The photo was captured at a distance.
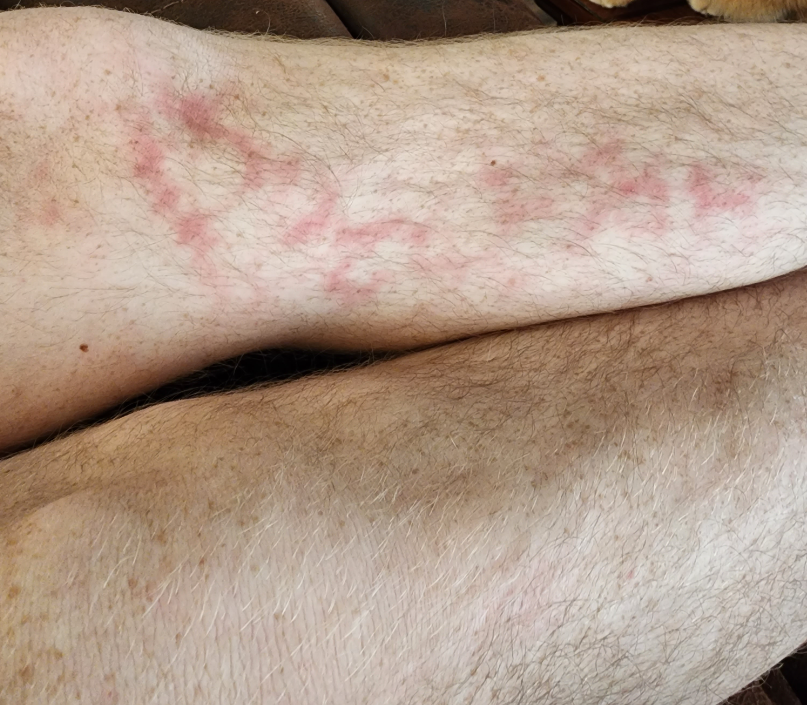Skin tone: Fitzpatrick phototype III.
On teledermatology review, the differential is split between Livedo reticularis and Erythema ab igne.